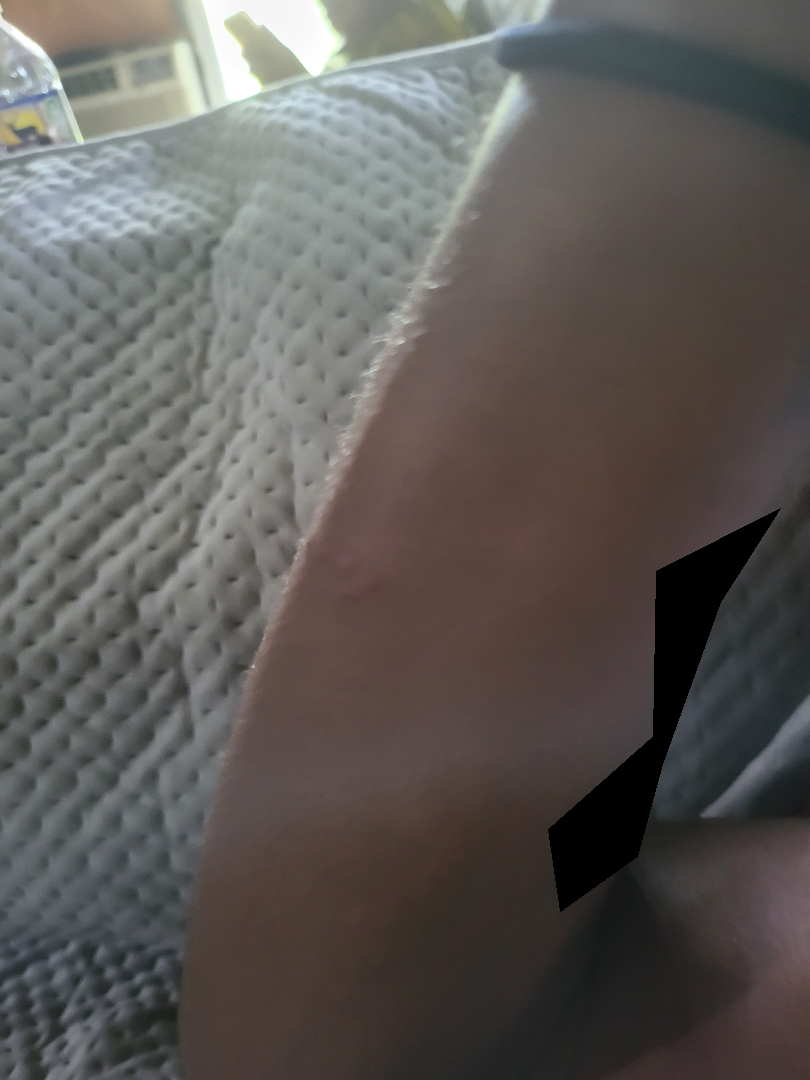The dermatologist could not determine a likely condition from the photograph alone.